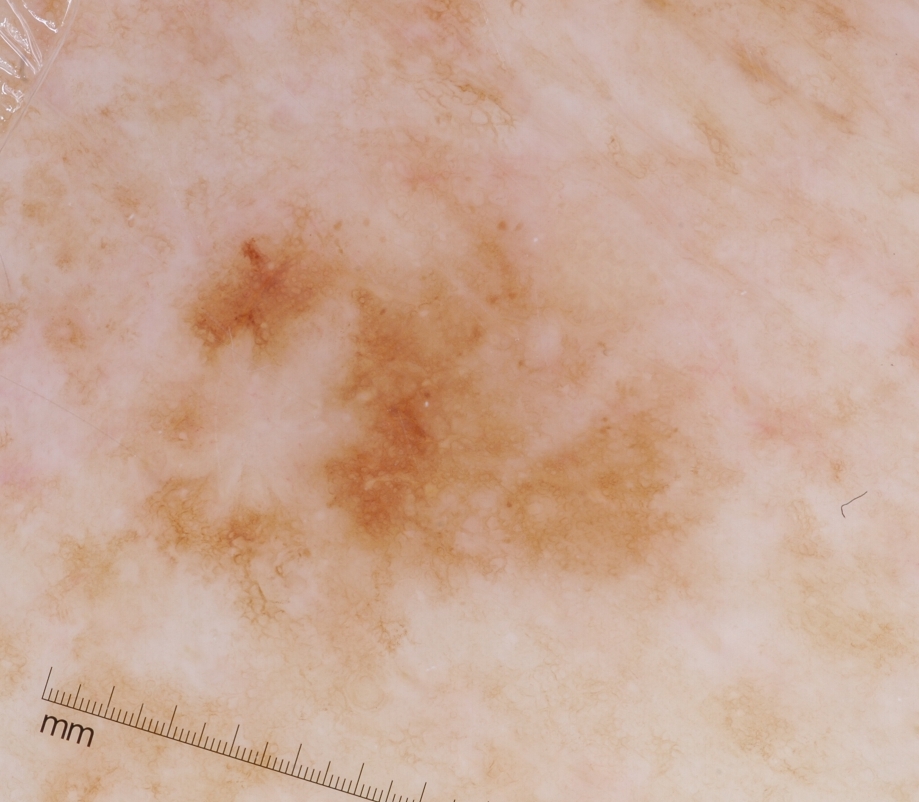image — dermoscopic image
lesion size — moderate
dermoscopic findings — milia-like cysts, pigment network, and globules; absent: negative network and streaks
lesion location — left=118, top=127, right=719, bottom=668
diagnosis — a melanoma, a malignant skin lesion